A female subject aged 78 to 82 — 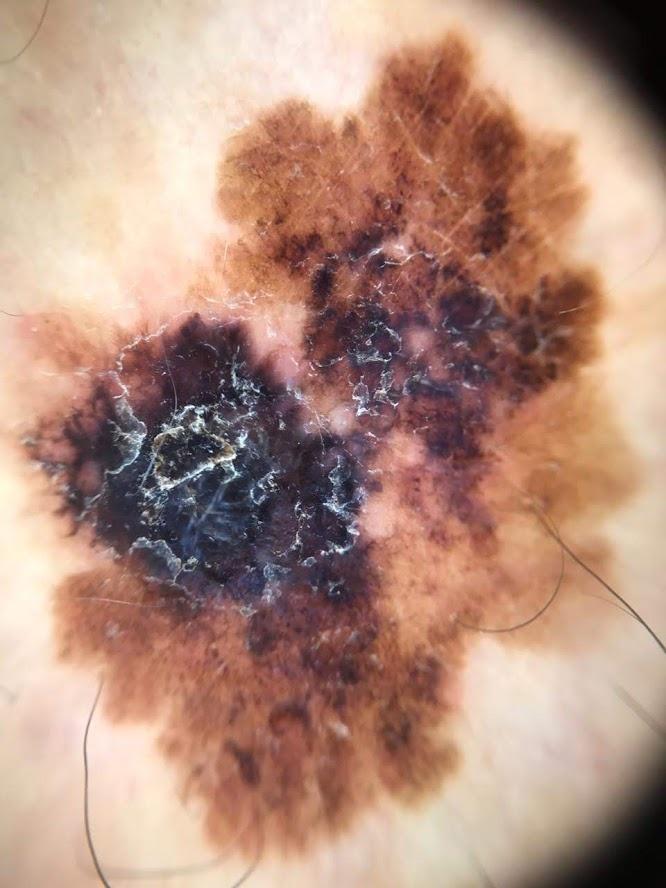Clinical context:
The lesion is on a lower extremity.
Conclusion:
Histopathological examination showed a malignancy — a melanoma.